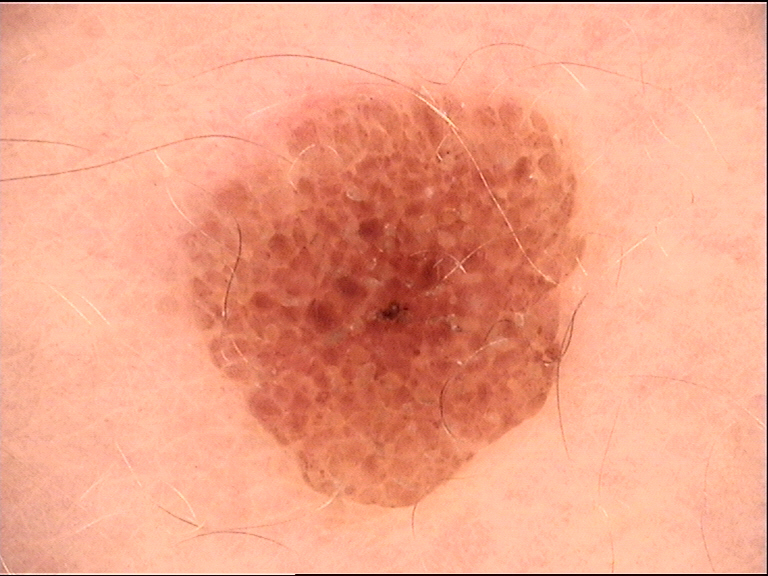label — compound nevus (expert consensus).